A dermatoscopic image of a skin lesion.
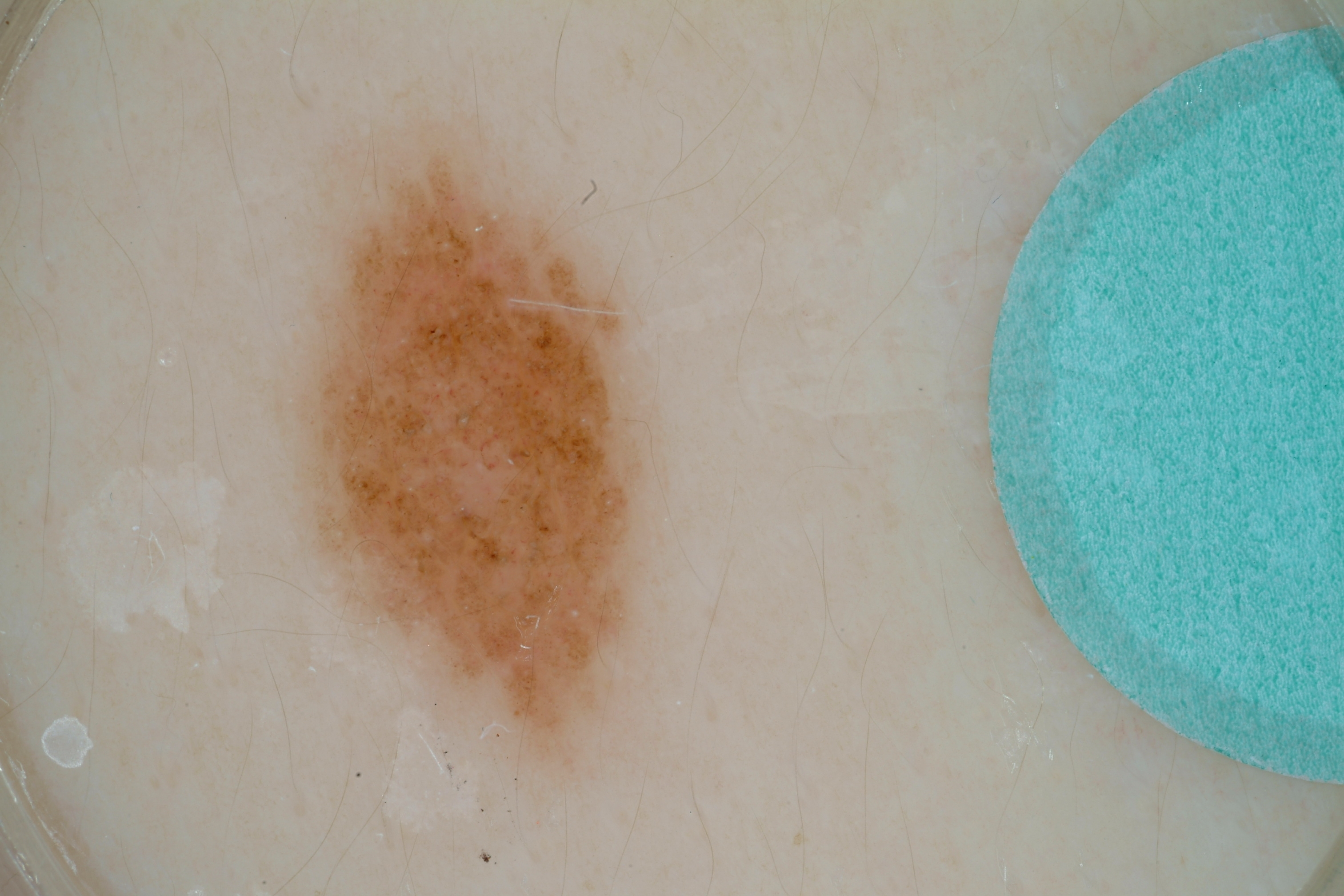Q: What is the lesion's bounding box?
A: 275/123/659/775
Q: What is this lesion?
A: a melanocytic nevus